The affected area is the arm, leg, palm, head or neck, front of the torso, back of the hand and back of the torso. The contributor is male. The photograph is a close-up of the affected area: 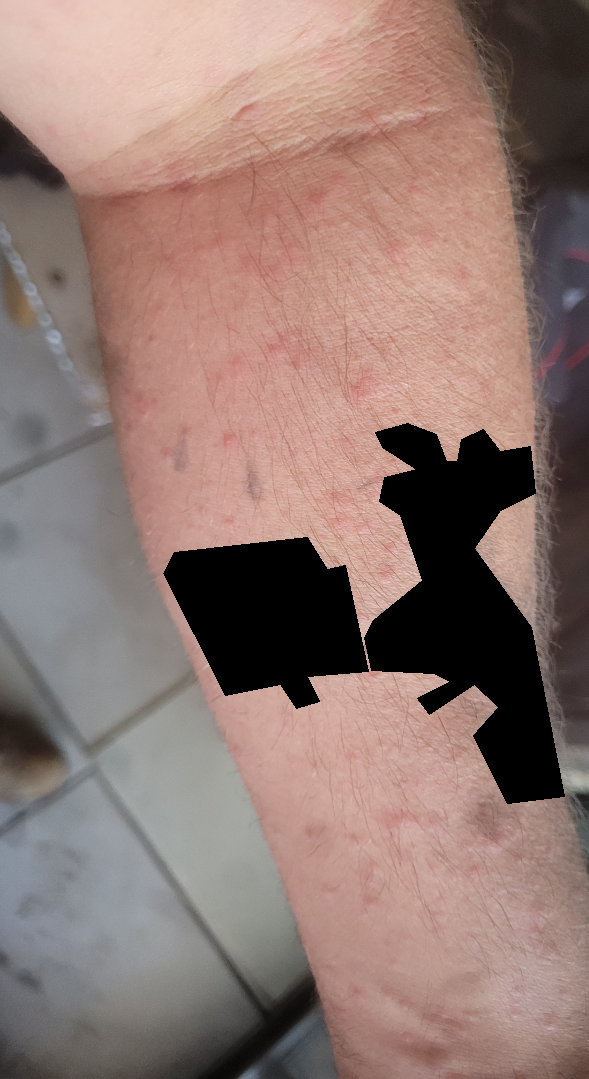Impression: Most consistent with Contact dermatitis.